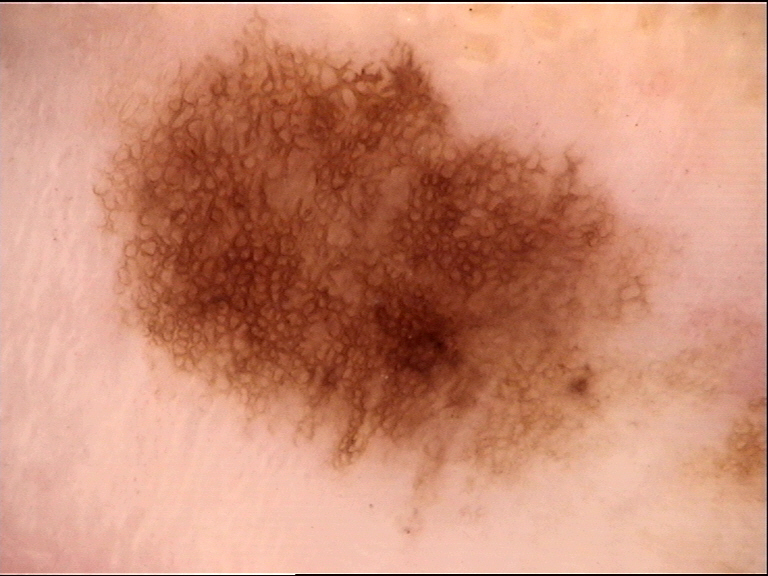modality = dermoscopy
assessment = dysplastic junctional nevus (expert consensus)